A dermoscopic close-up of a skin lesion — 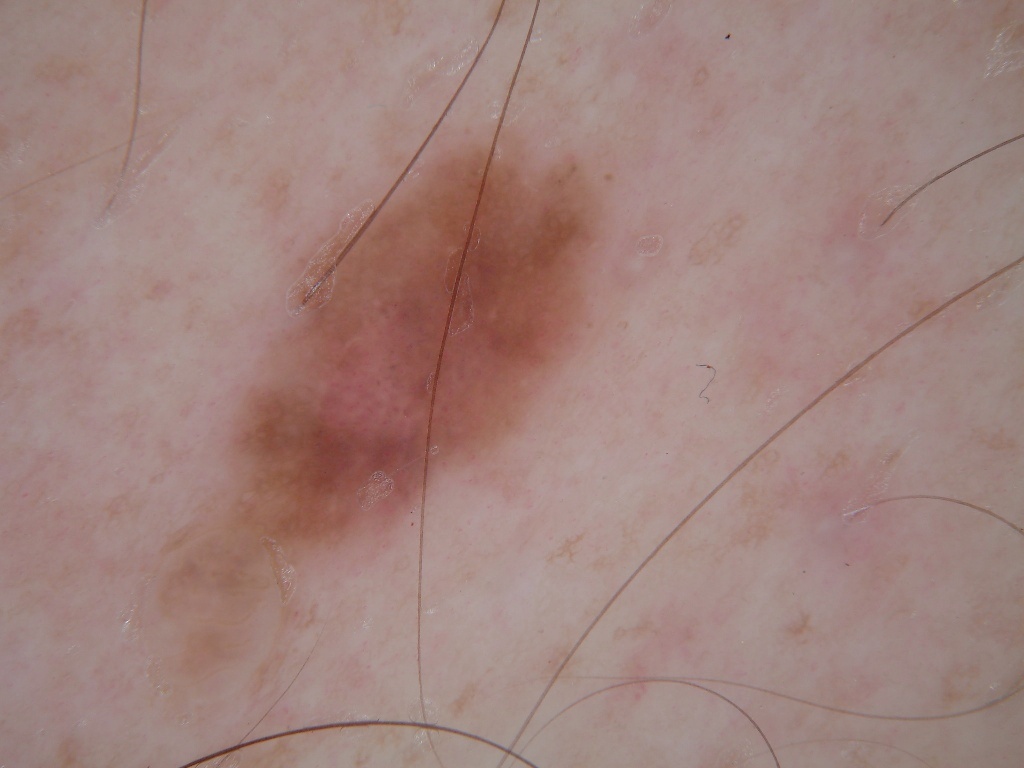Case summary:
In (x1, y1, x2, y2) order, the lesion is located at (154, 106, 624, 716). Dermoscopic review identifies pigment network and negative network; no streaks, milia-like cysts, or globules.
Assessment:
Diagnosed as a melanocytic nevus, a benign skin lesion.